The subject is male. The photograph was taken at a distance. The arm and leg are involved.
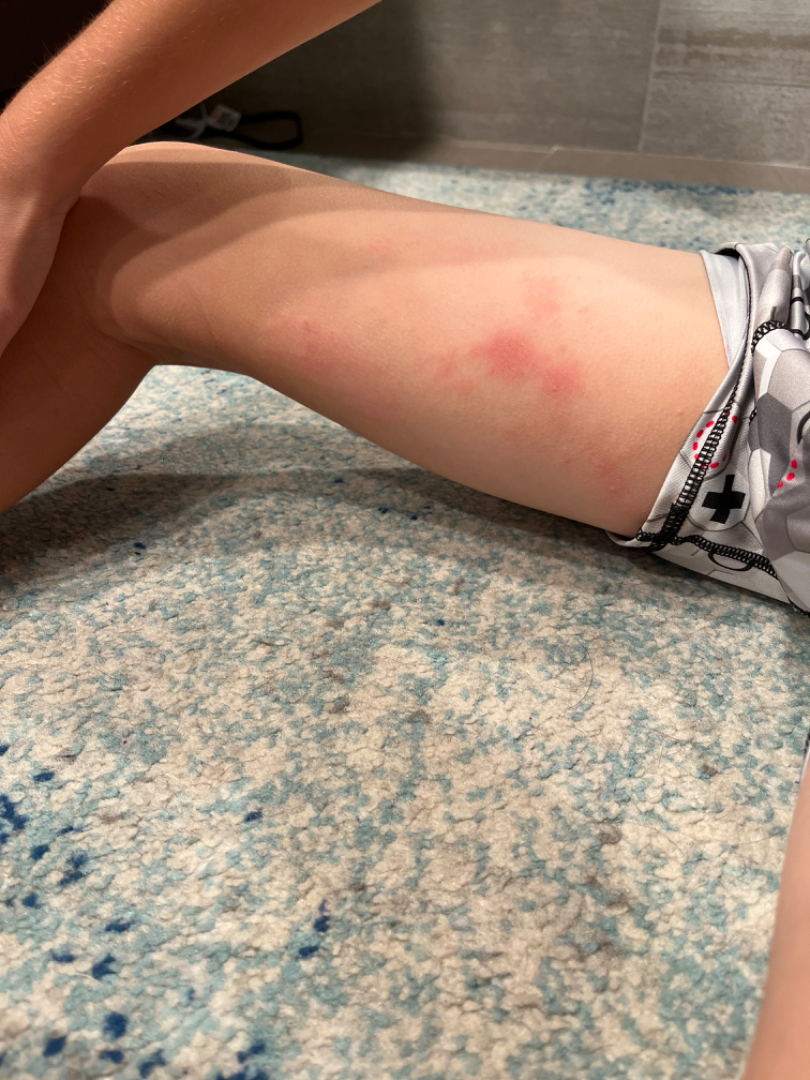The patient reports the lesion is raised or bumpy and rough or flaky.
Self-categorized by the patient as a rash.
Reported lesion symptoms include itching.
Present for less than one week.
No relevant systemic symptoms.
Most likely Eczema; with consideration of Irritant Contact Dermatitis.